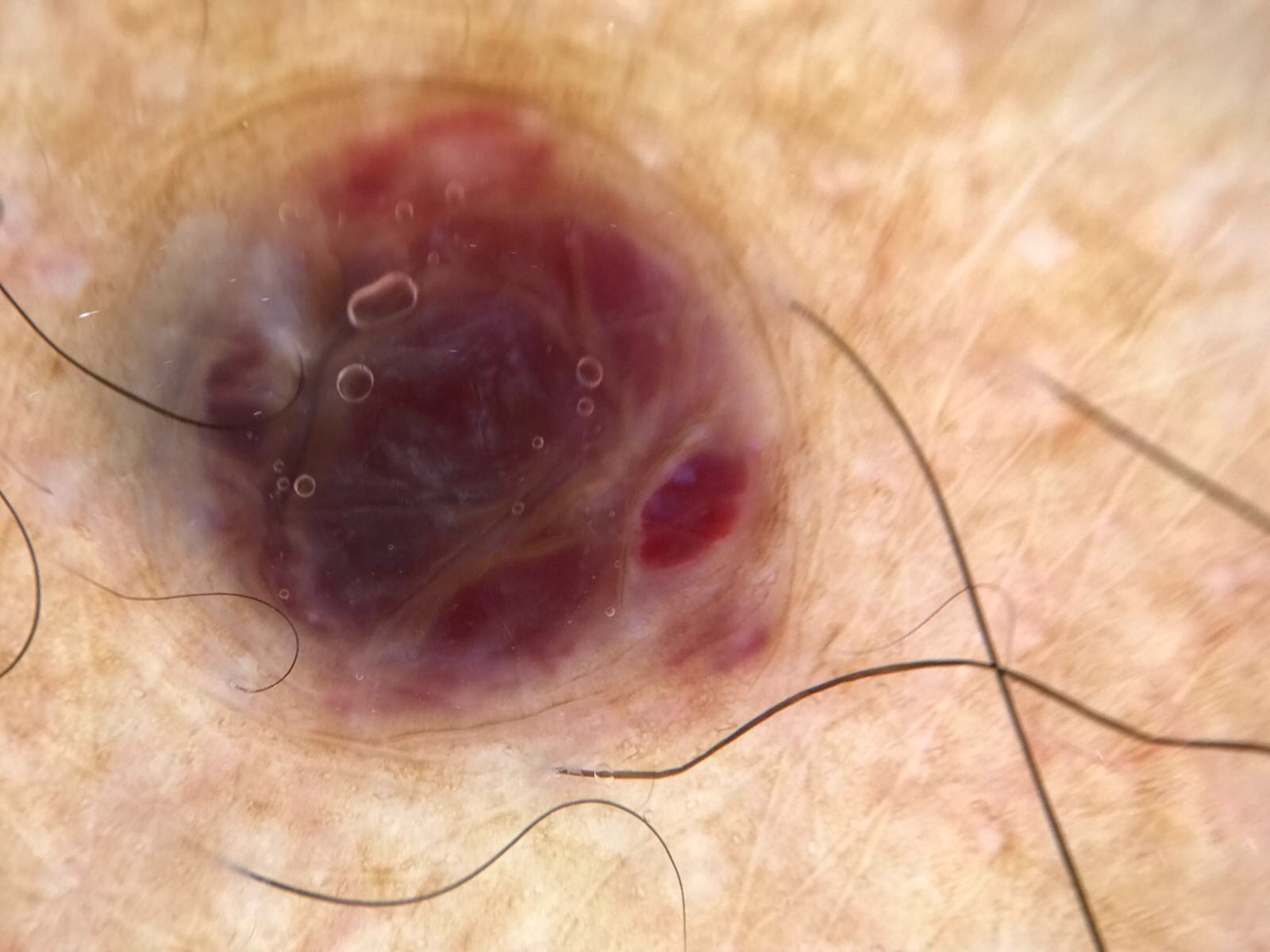<dermoscopy>
<image>dermoscopy</image>
<diagnosis>
<name>hemangioma</name>
<code>ha</code>
<malignancy>benign</malignancy>
<super_class>non-melanocytic</super_class>
<confirmation>expert consensus</confirmation>
</diagnosis>
</dermoscopy>